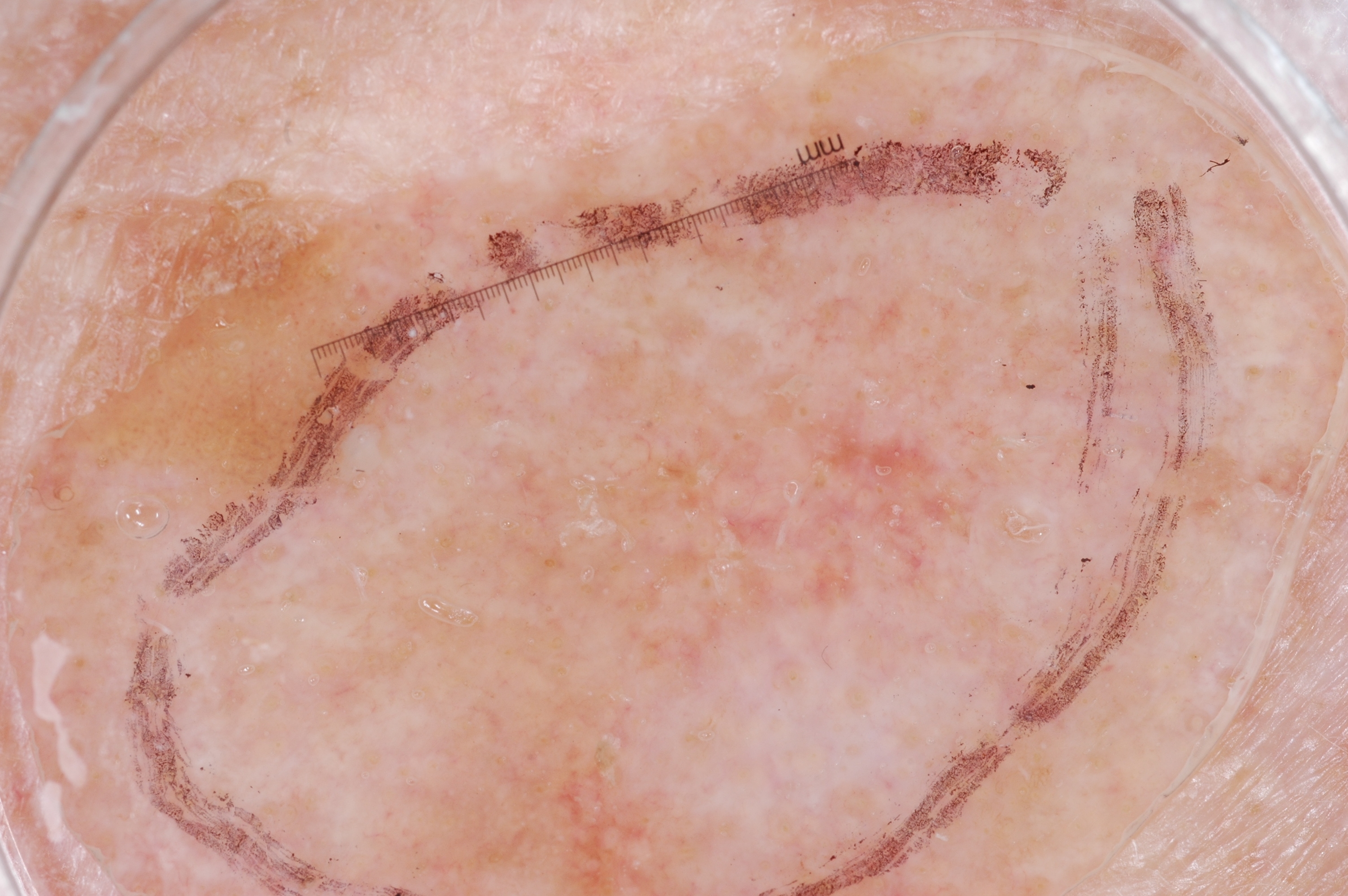{
  "image": {
    "modality": "dermoscopy"
  },
  "patient": {
    "sex": "male",
    "age_approx": 70
  },
  "lesion_location": {
    "bbox_xyxy": [
      165,
      168,
      1193,
      894
    ]
  },
  "dermoscopic_features": {
    "present": [],
    "absent": [
      "negative network",
      "streaks",
      "pigment network",
      "milia-like cysts"
    ]
  },
  "diagnosis": {
    "name": "seborrheic keratosis",
    "malignancy": "benign",
    "lineage": "keratinocytic",
    "provenance": "clinical"
  }
}